This image was taken at an angle; the back of the hand, leg, top or side of the foot, palm and arm are involved: 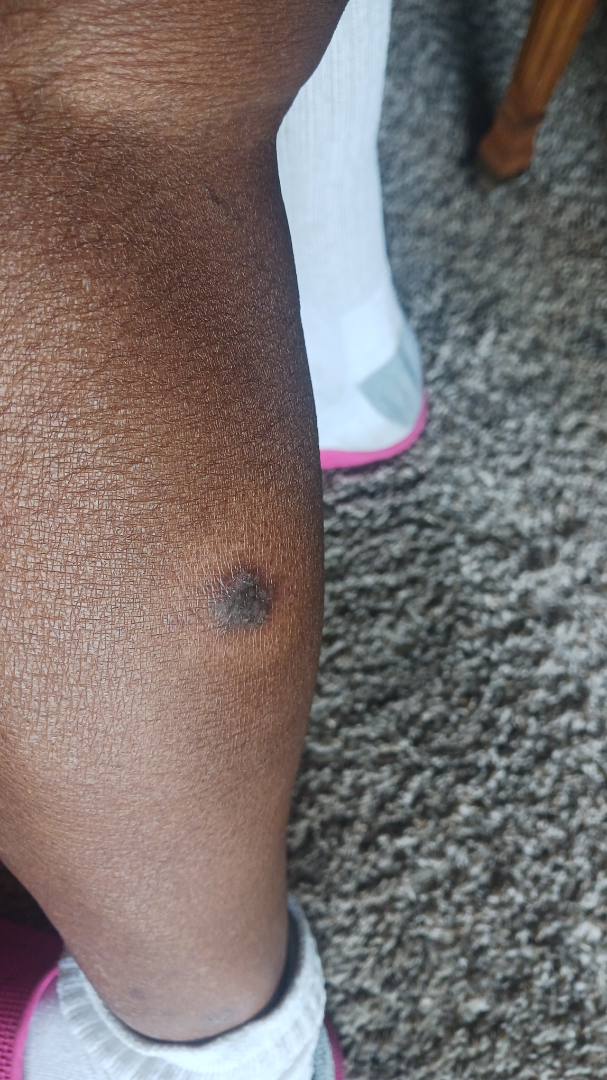Q: Could the case be diagnosed?
A: unable to determine
Q: How does the patient describe it?
A: a pigmentary problem
Q: Texture?
A: flat and raised or bumpy
Q: Reported symptoms?
A: bothersome appearance, darkening and itching
Q: Fitzpatrick or Monk tone?
A: Fitzpatrick VI; lay graders estimated Monk Skin Tone 6 or 8